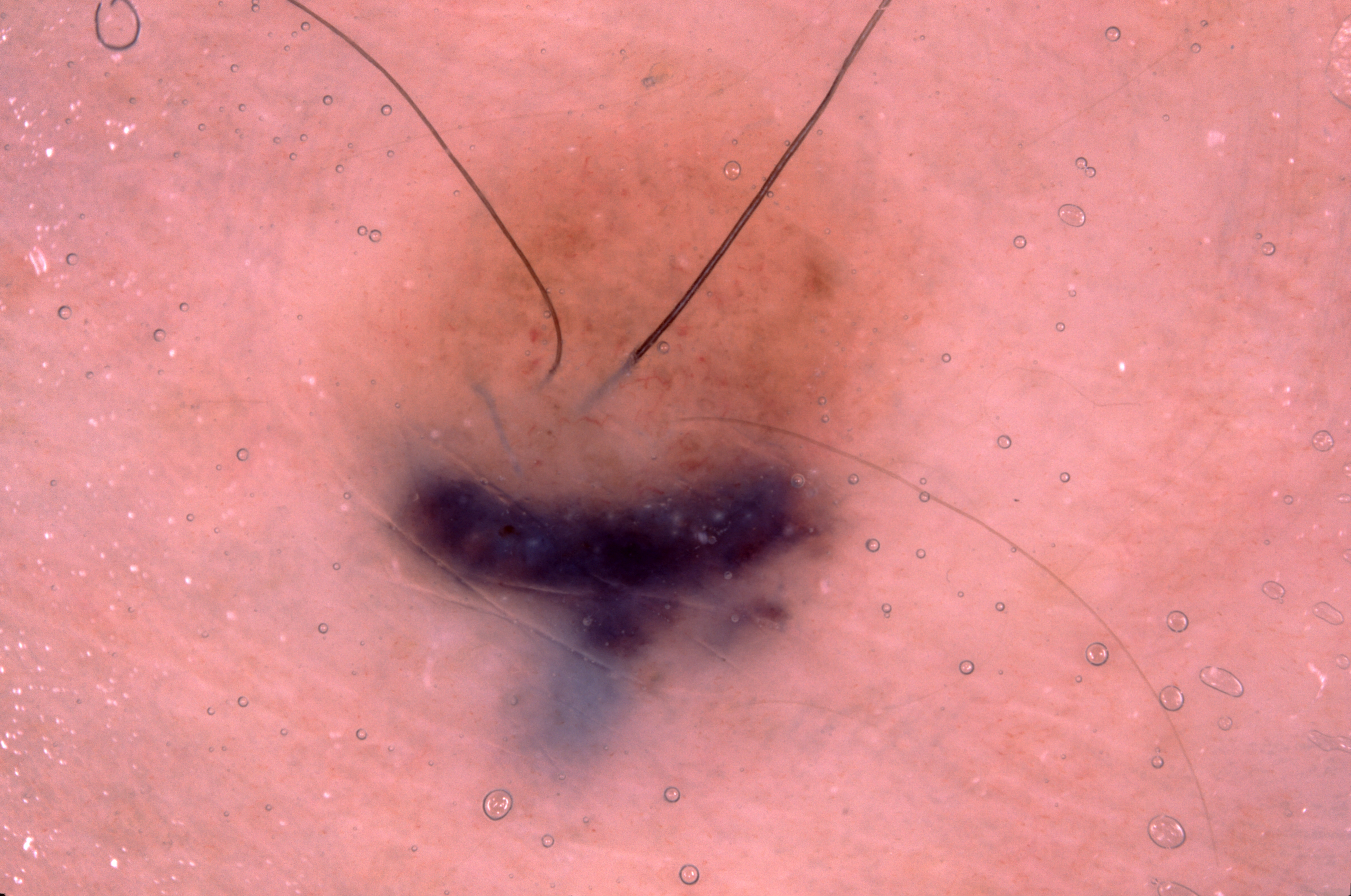A female subject, approximately 50 years of age. A dermatoscopic image of a skin lesion. On dermoscopy, the lesion shows no streaks, pigment network, negative network, or milia-like cysts. The lesion covers approximately 32% of the dermoscopic field. As (left, top, right, bottom), the visible lesion spans bbox(294, 41, 964, 821). The lesion was assessed as a melanocytic nevus.